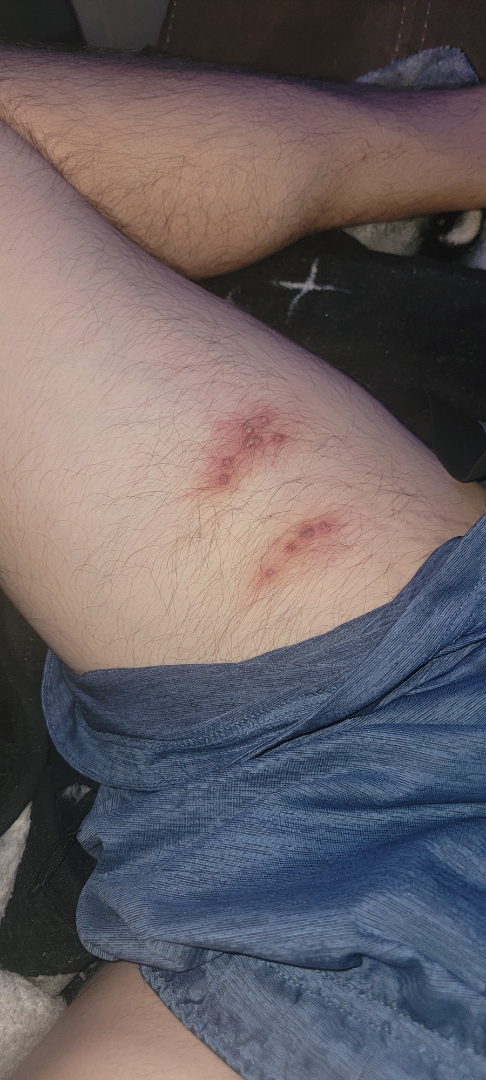Q: Patient demographics?
A: male, age 30–39
Q: Image view?
A: at a distance
Q: What symptoms does the patient report?
A: itching and bothersome appearance
Q: How long has this been present?
A: less than one week
Q: Where on the body?
A: leg
Q: How does the lesion feel?
A: fluid-filled
Q: What is the dermatologist's impression?
A: a single dermatologist reviewed the case: Herpes Zoster and Herpes Simplex were each considered, in no particular order; less probable is Impetigo